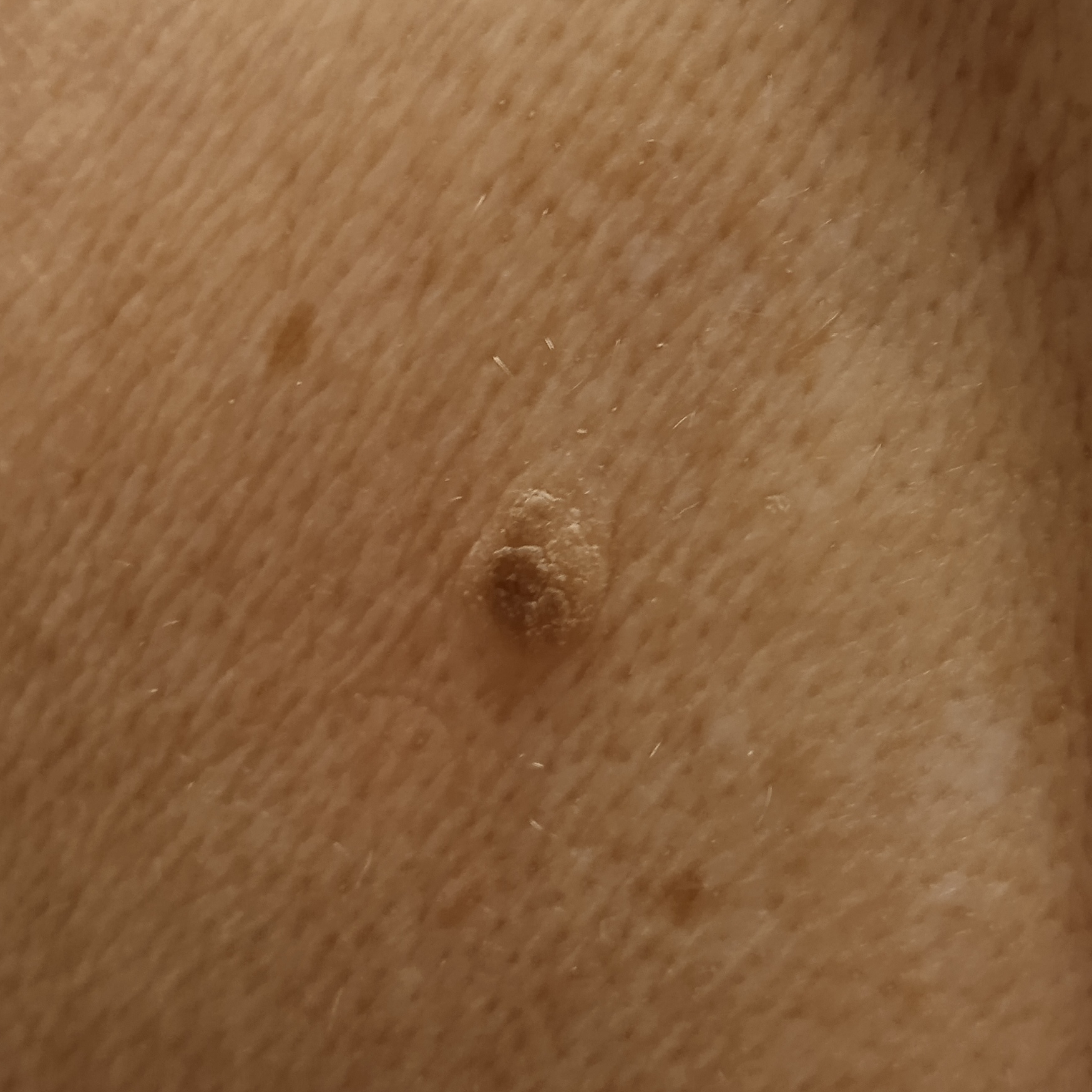patient:
  age: 73
  sex: female
image: clinical photograph
referral: research study (no referral diagnosis)
lesion_location: the back
lesion_size:
  diameter_mm: 8.6
diagnosis:
  name: seborrheic keratosis
  malignancy: benign